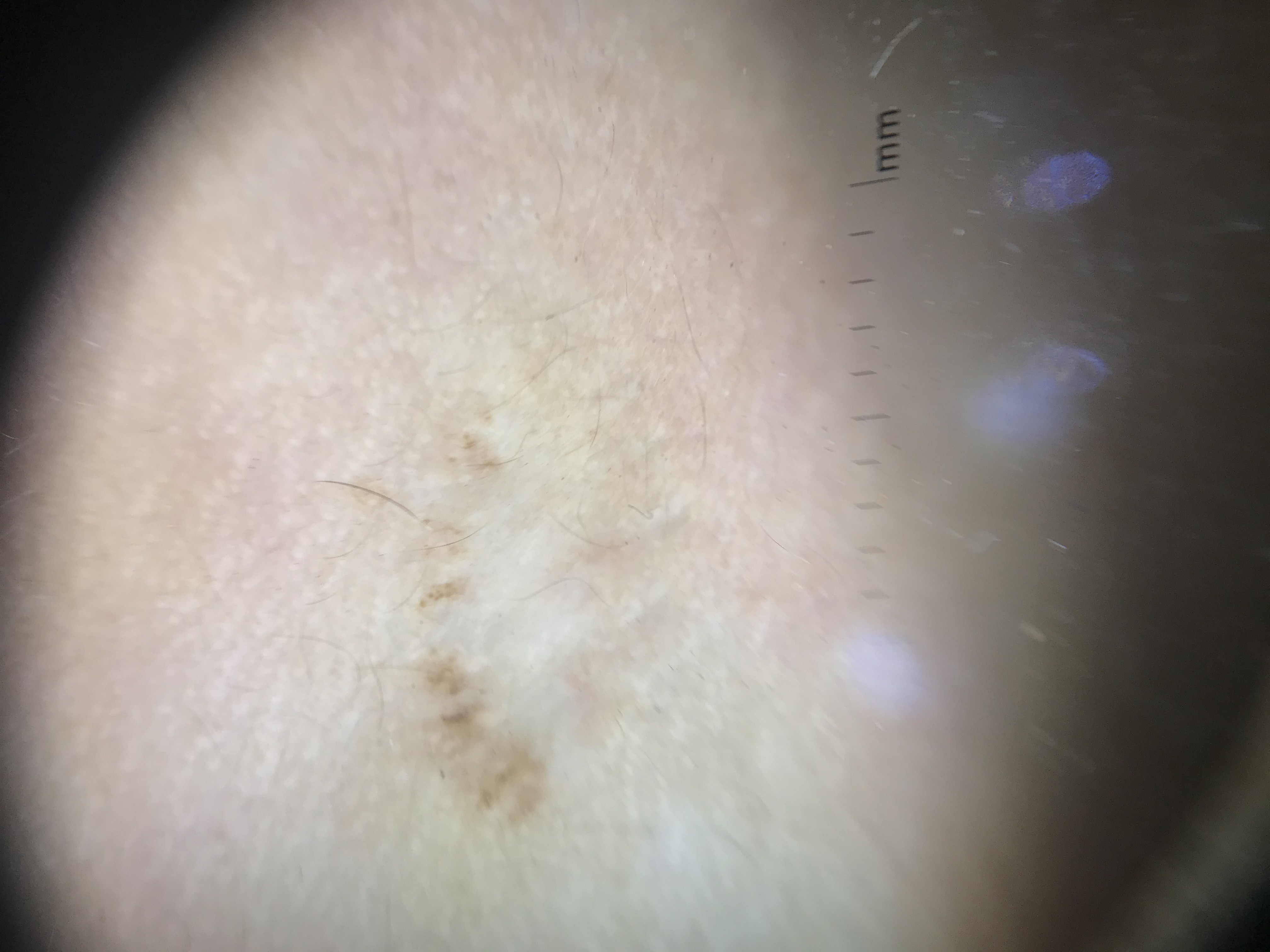Conclusion:
Consistent with a recurrent nevus.